A dermoscopy image of a single skin lesion.
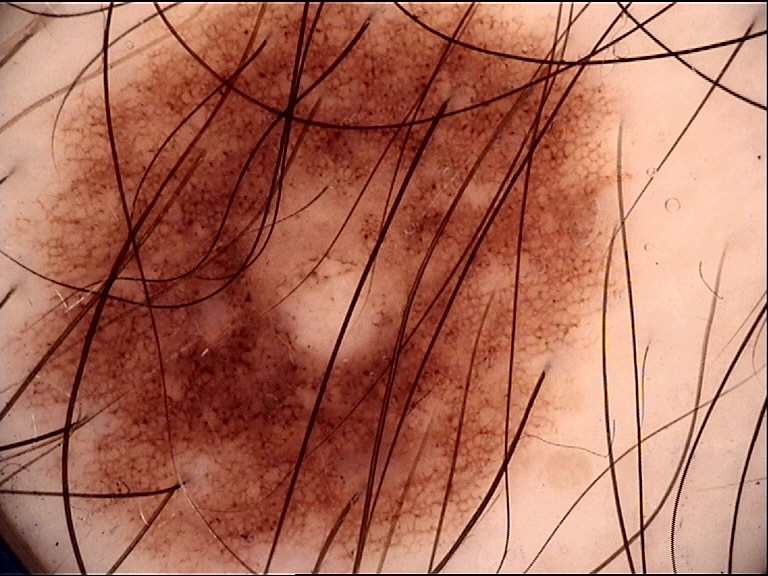Consistent with a benign lesion — a dysplastic junctional nevus.